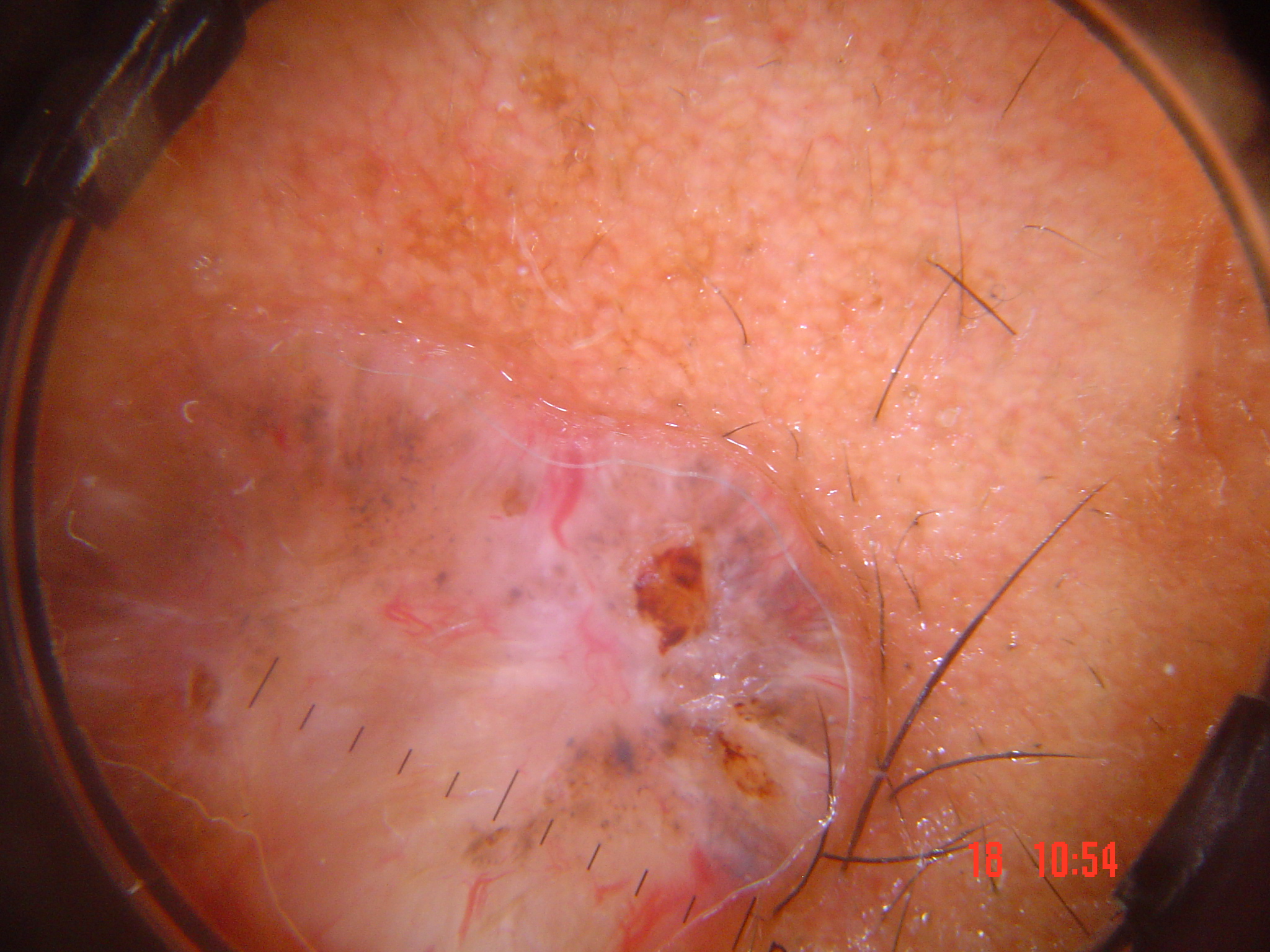A dermoscopy image of a single skin lesion. Confirmed on histopathology as a skin cancer — a basal cell carcinoma.